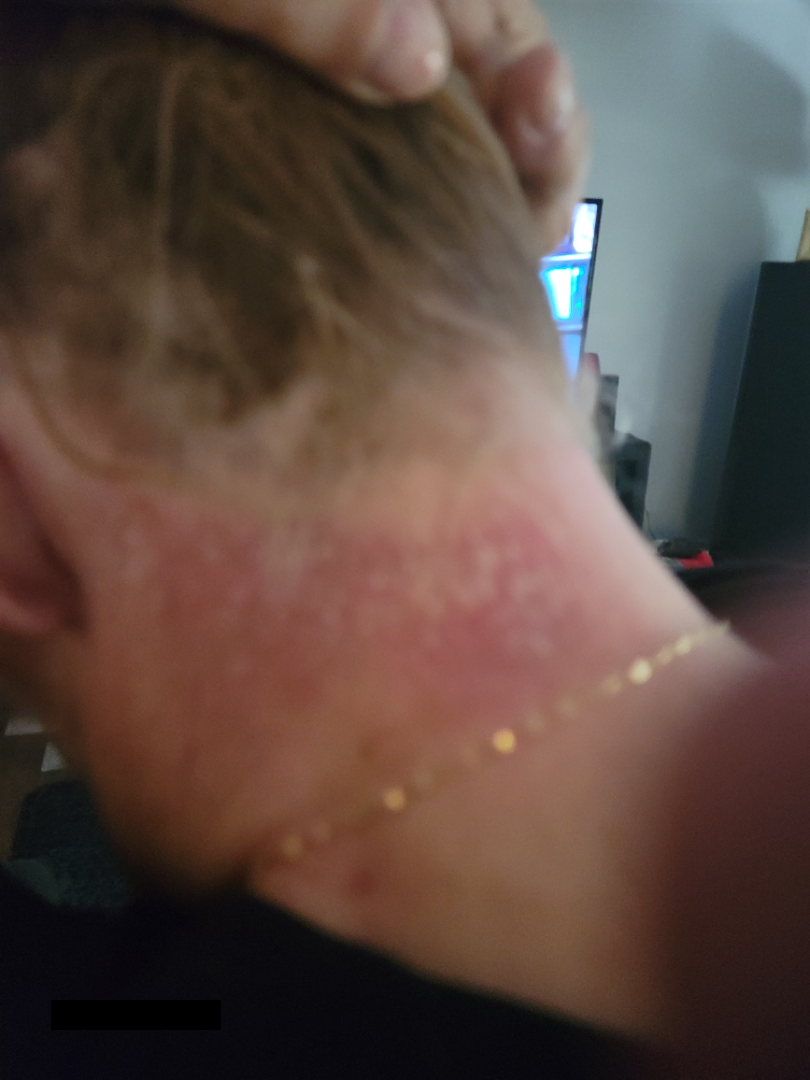image framing: at a distance | impression: favoring Psoriasis; also raised was Eczema.